The patient was assessed as Fitzpatrick III · the chart documents a first-degree relative with melanoma · a dermoscopy image of a single skin lesion.
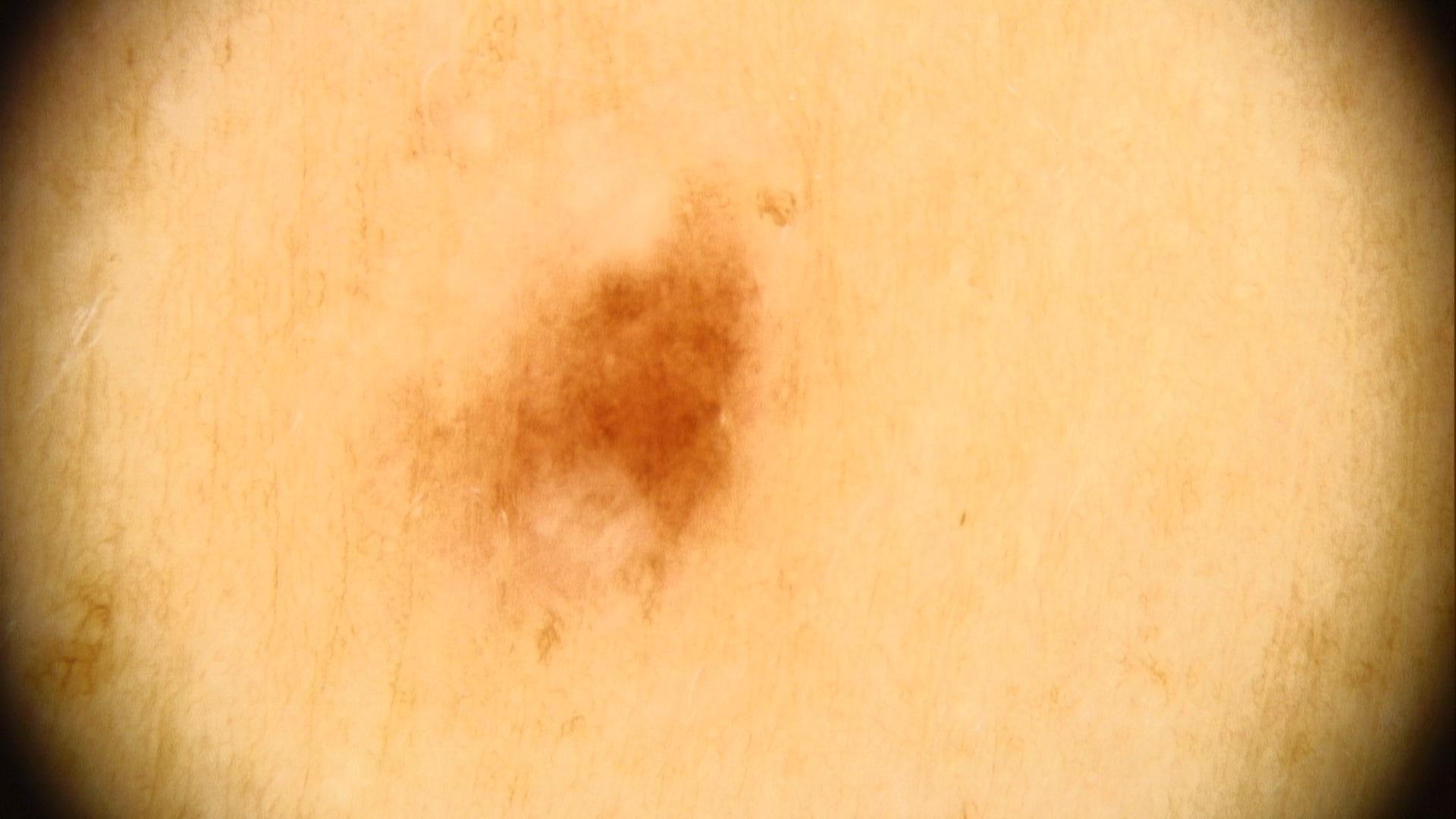The lesion involves the trunk, specifically the posterior trunk. The diagnostic impression was a benign, melanocytic lesion — a nevus.